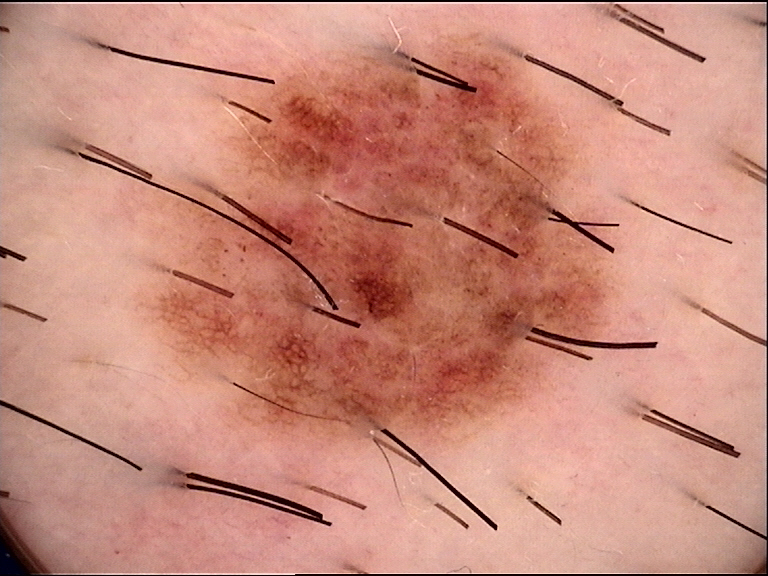Diagnosed as a benign lesion — a dysplastic compound nevus.